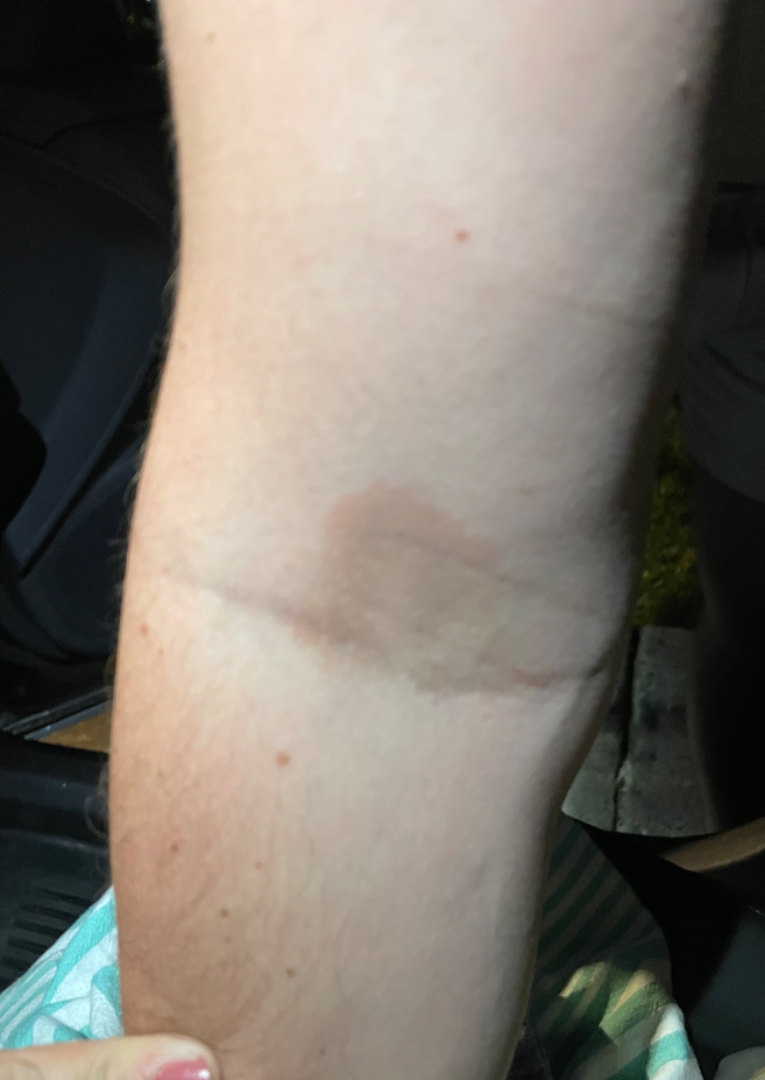<case>
<assessment>indeterminate</assessment>
<duration>less than one week</duration>
<body_site>arm</body_site>
<patient>male, age 18–29</patient>
<shot_type>close-up</shot_type>
<systemic_symptoms>none reported</systemic_symptoms>
<texture>flat</texture>
</case>